The lesion is described as raised or bumpy · a close-up photograph · located on the arm and leg · the condition has been present for one to four weeks · the lesion is associated with itching · lay graders estimated a MST of 3.
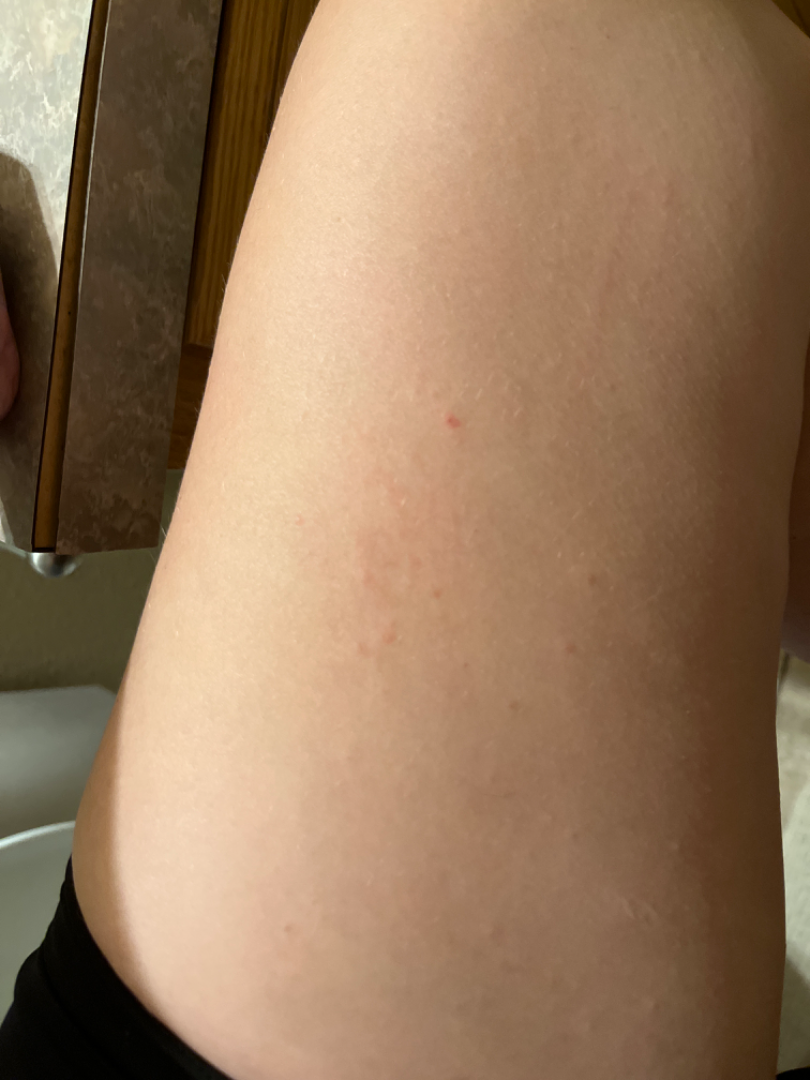Findings: The skin findings could not be characterized from the image.